A male subject aged 38 to 42; a dermoscopy image of a single skin lesion: 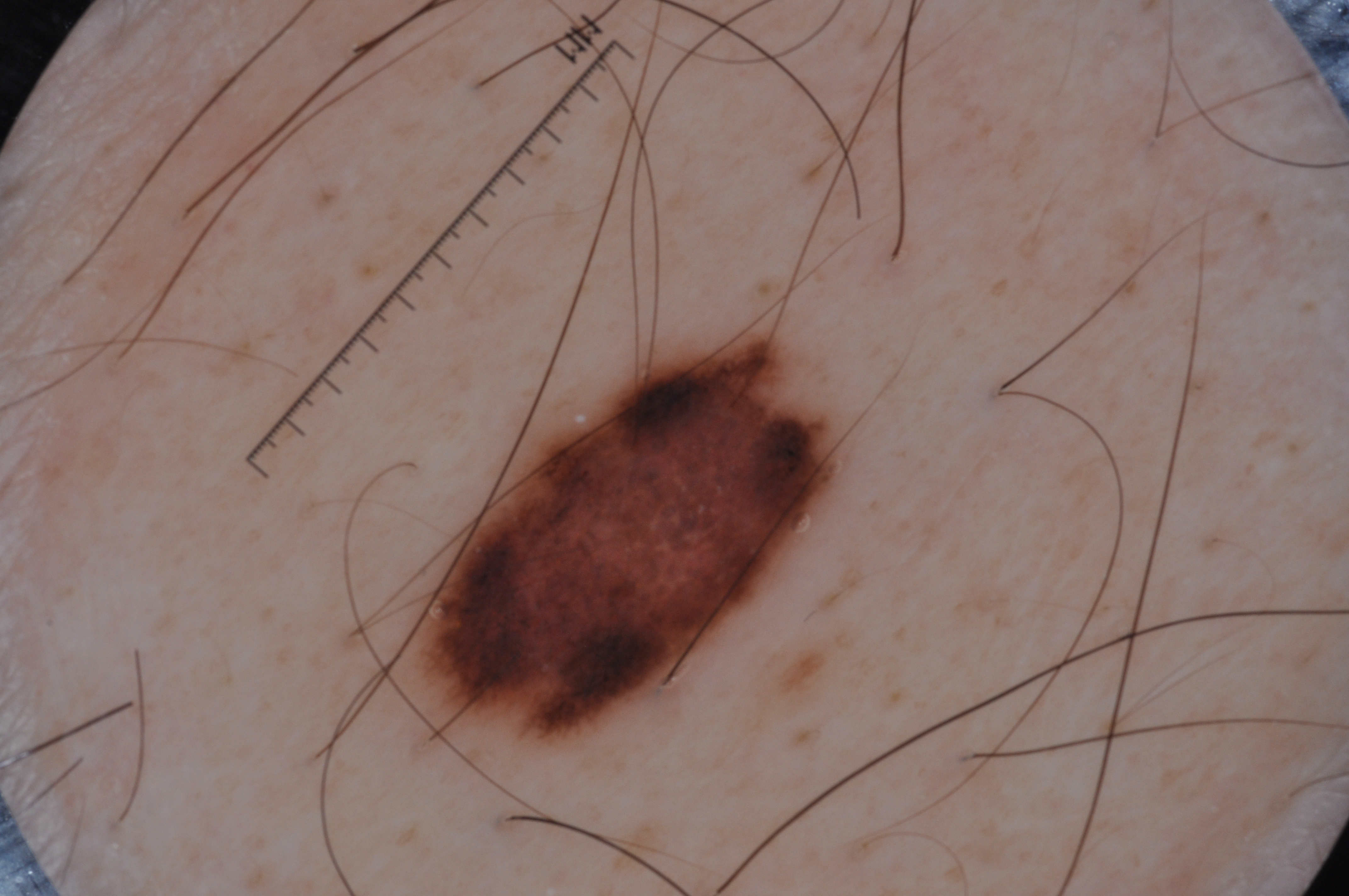lesion extent = ~11% of the field
dermoscopic features = pigment network, negative network, and milia-like cysts; absent: streaks
lesion location = left=411, top=307, right=848, bottom=759
diagnosis = a melanocytic nevus